A dermoscopy image of a single skin lesion.
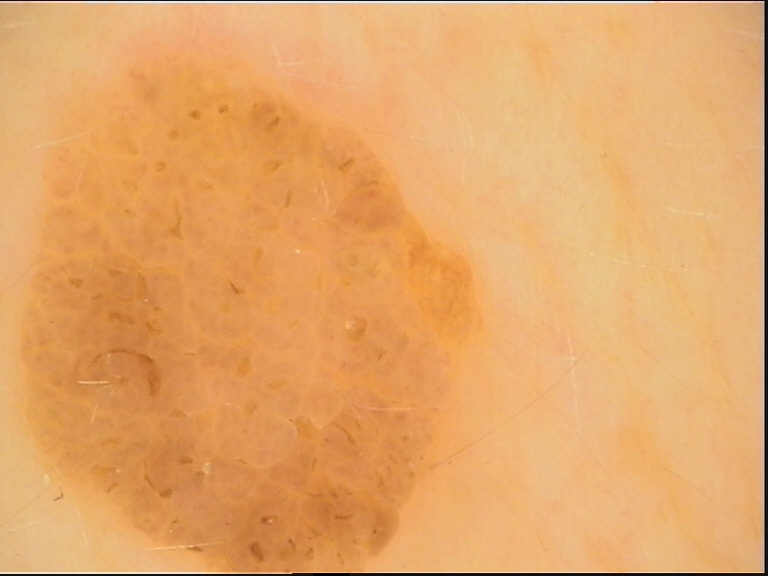Classified as a banal lesion — a compound nevus.